The lesion involves the arm and leg · the contributor is female · this is a close-up image.
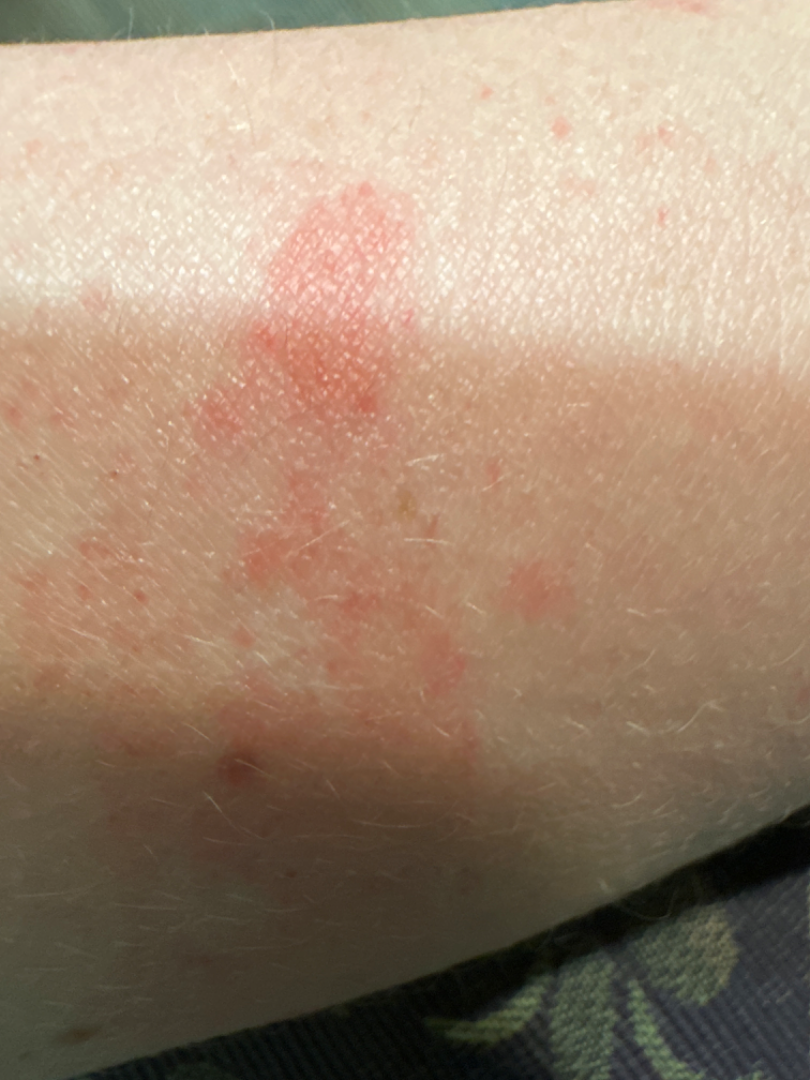Assessment:
The favored diagnosis is Eczema.